Collected as part of a research study, without a referral diagnosis; a moderate number of moles by the patient's own estimate: 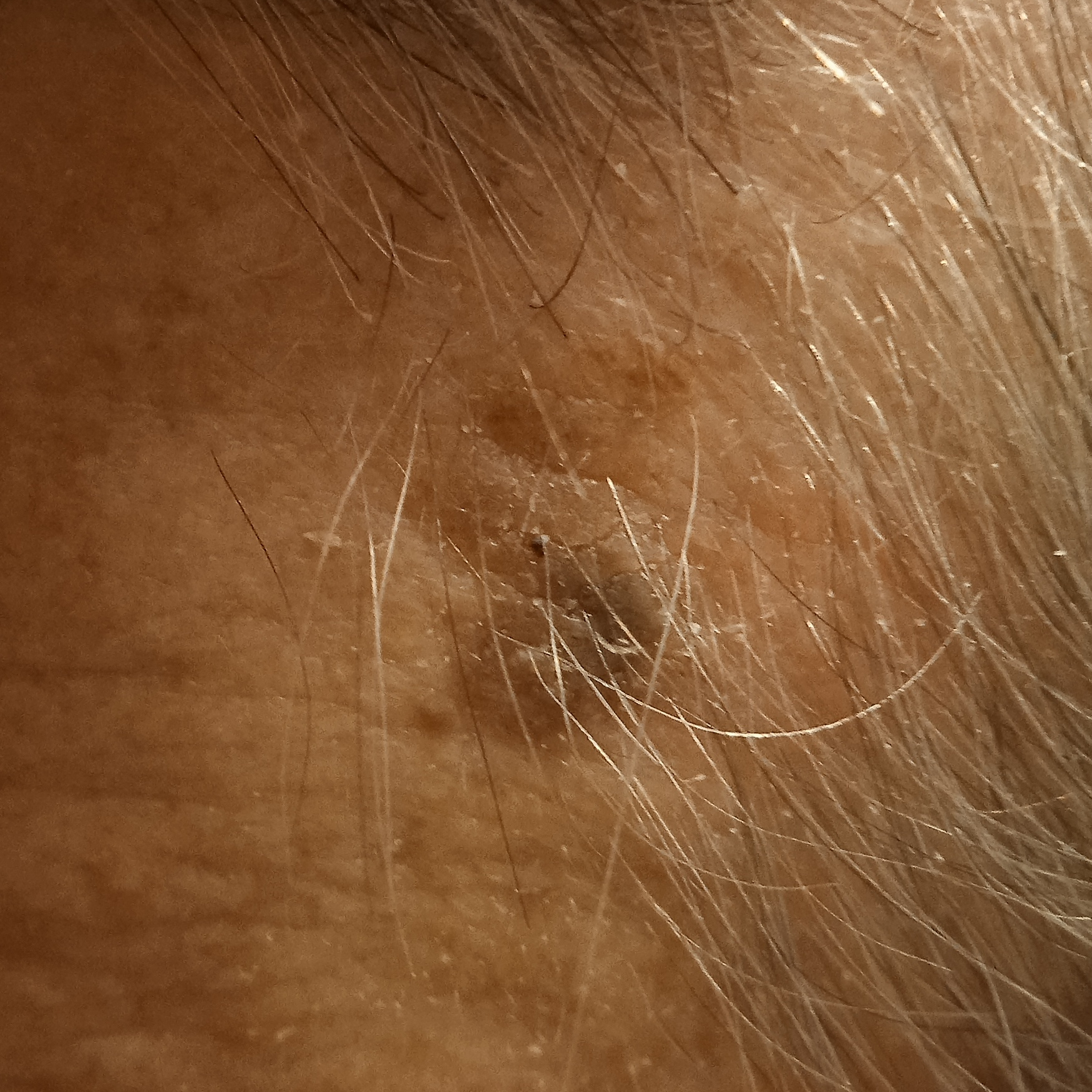The lesion is located on an arm. The lesion is about 7.3 mm across. On independent review by four dermatologists, the agreed diagnosis was a seborrheic keratosis; diagnostic confidence was moderate.